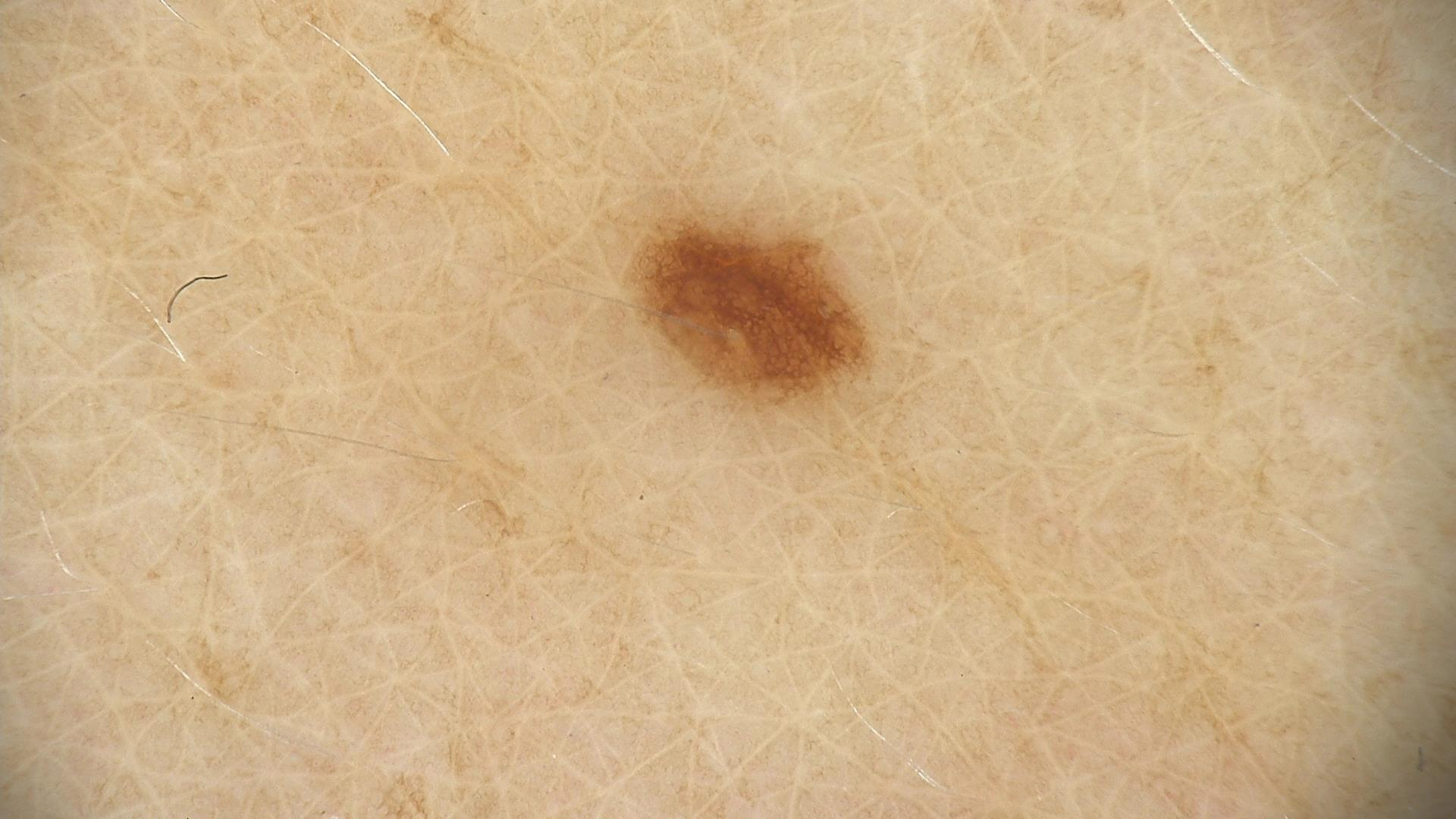A dermoscopic photograph of a skin lesion. Consistent with a dysplastic junctional nevus.